The lesion involves the back of the torso · the photo was captured at a distance:
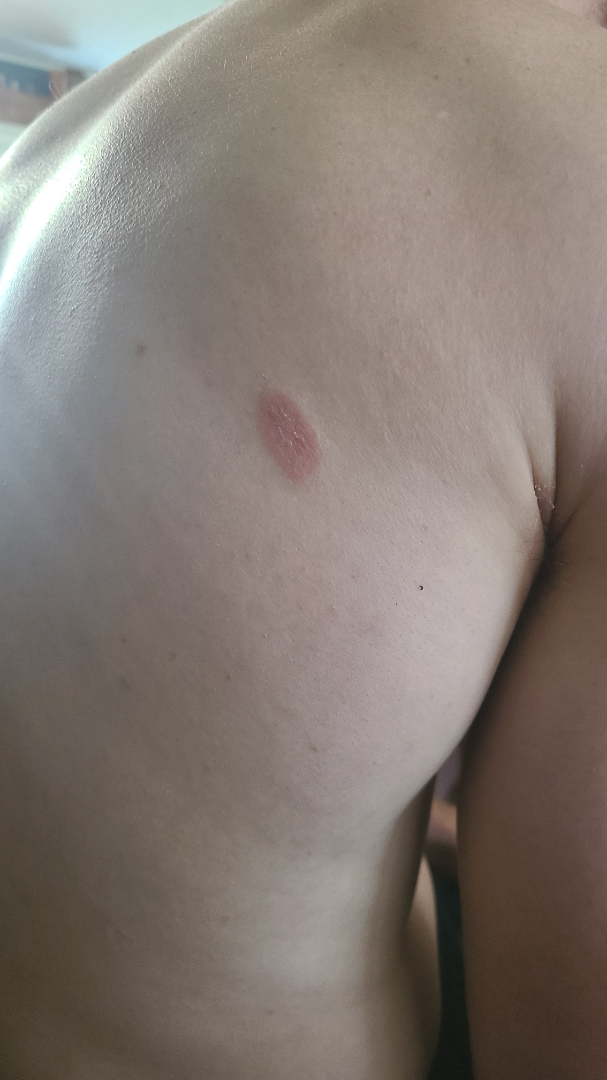Symptoms reported: bothersome appearance.
The condition has been present for one to four weeks.
On remote review of the image: the favored diagnosis is Pityriasis rosea.